A dermatoscopic image of a skin lesion.
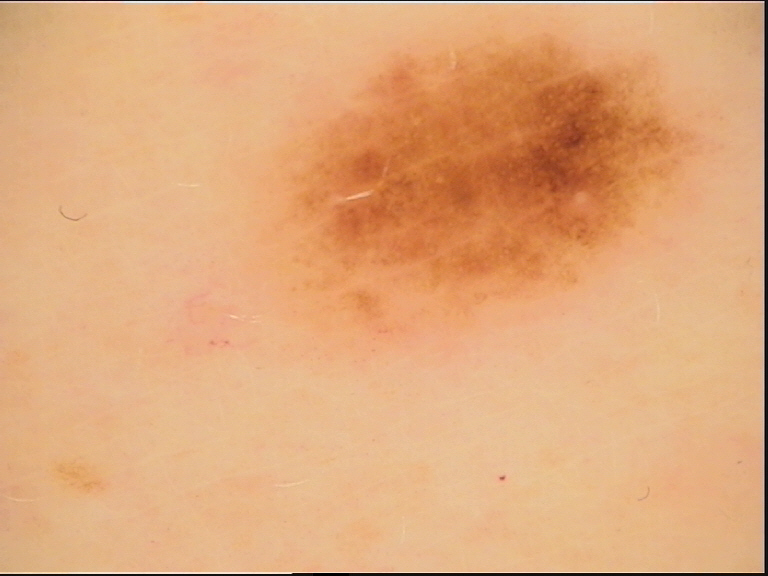Q: What is the diagnosis?
A: dysplastic junctional nevus (expert consensus)